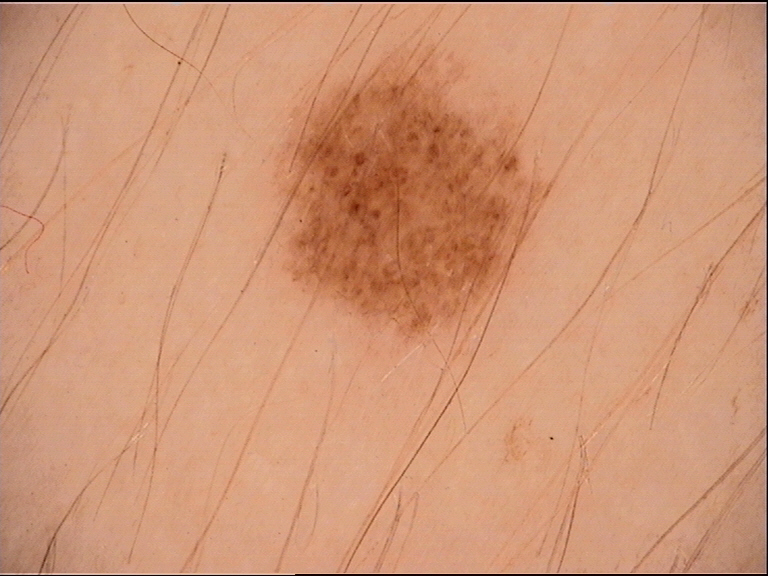A dermatoscopic image of a skin lesion. Classified as a benign lesion — a dysplastic junctional nevus.